Present for about one day. The lesion is associated with itching. The patient considered this a rash. The photo was captured at an angle. The lesion is described as raised or bumpy. No relevant systemic symptoms. The lesion involves the arm — 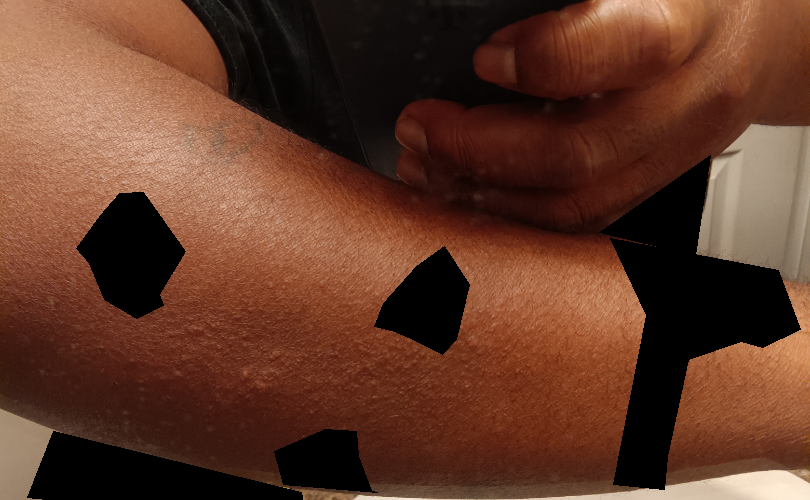  differential:
    tied_lead:
      - Lichen spinulosus
      - Eczema
    unlikely:
      - Keratosis pilaris